Located on the leg · this is a close-up image:
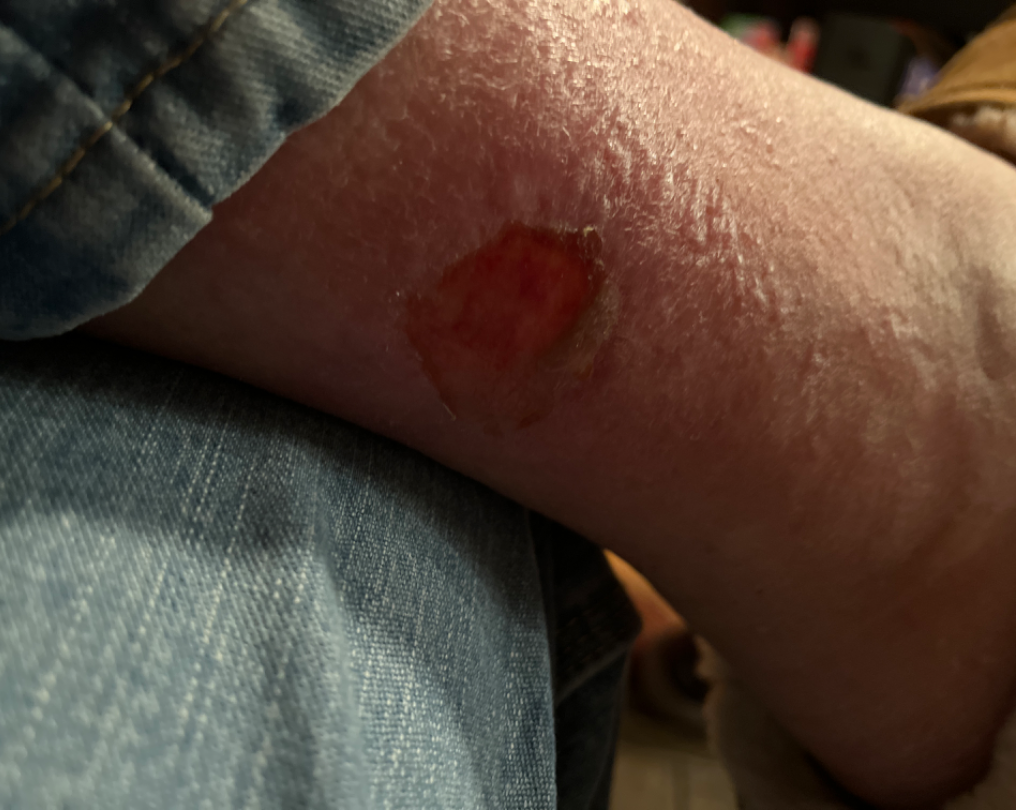* assessment: Erosion of skin (possible); Abrasion, scrape, or scab (possible); Traumatic blister (possible)